A dermoscopic image of a skin lesion: 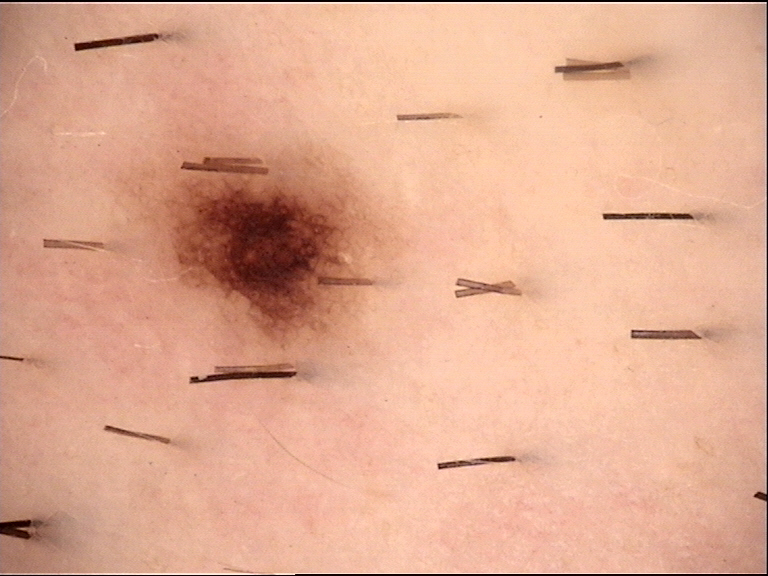Impression:
The diagnosis was a benign lesion — a dysplastic junctional nevus.